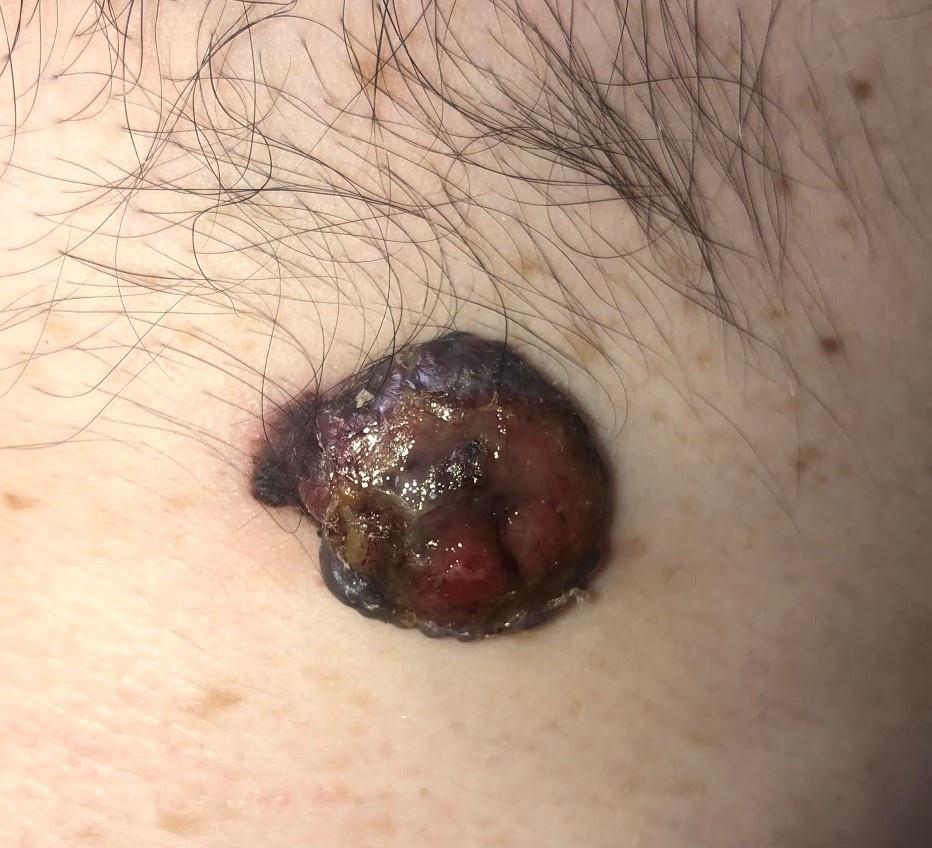Per the chart, a previous melanoma.
A male patient about 50 years old.
A clinical photograph showing a skin lesion in context.
The patient was assessed as Fitzpatrick skin type II.
The lesion involves the trunk.
Confirmed on histopathology as a melanoma.